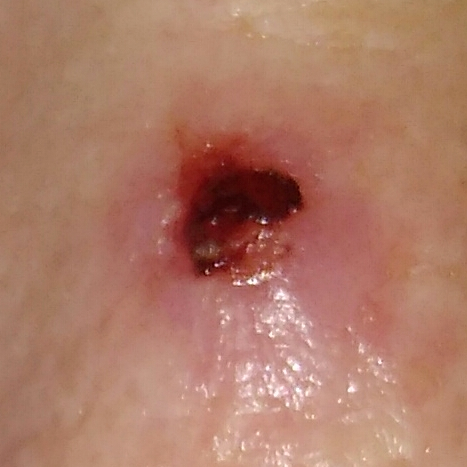– subject · female, 55 years of age
– skin type · II
– exposure history · prior malignancy (patient or family)
– image type · clinical photograph
– region · the nose
– diameter · 7 × 5 mm
– reported symptoms · bleeding, elevation, pain, growth, itching / no change in appearance
– diagnostic label · basal cell carcinoma (biopsy-proven)